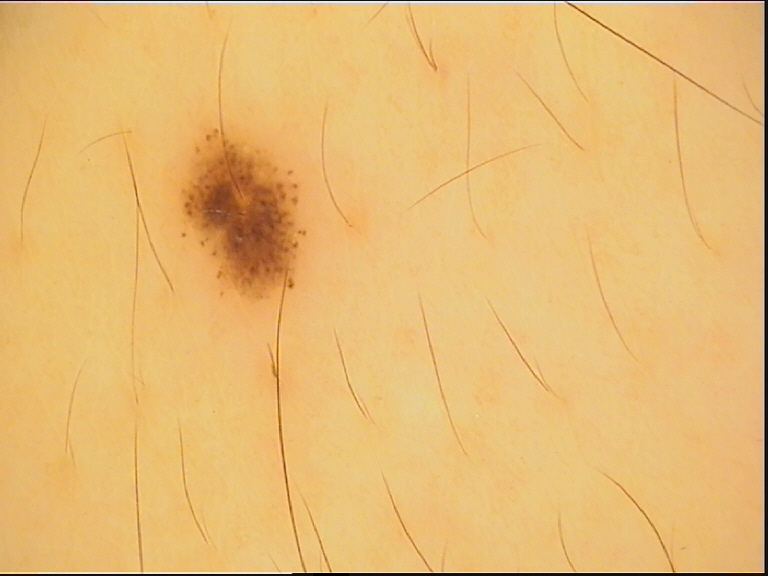Diagnosed as a dysplastic junctional nevus.